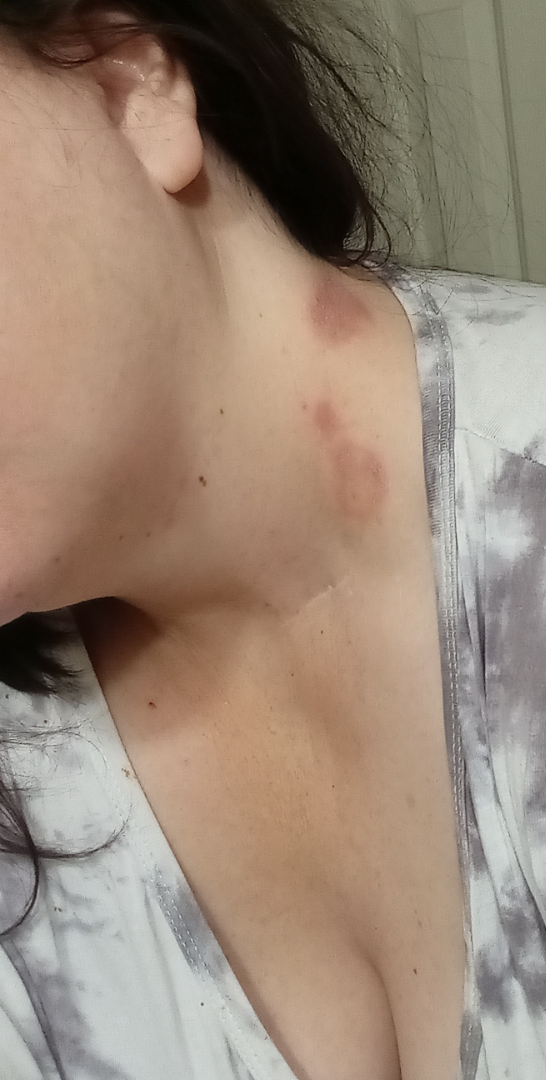{"assessment": "ungradable on photographic review", "shot_type": "close-up", "symptoms": ["itching", "burning", "darkening", "enlargement", "pain"], "duration": "three to twelve months", "texture": "fluid-filled", "patient_category": "a rash", "body_site": "head or neck"}